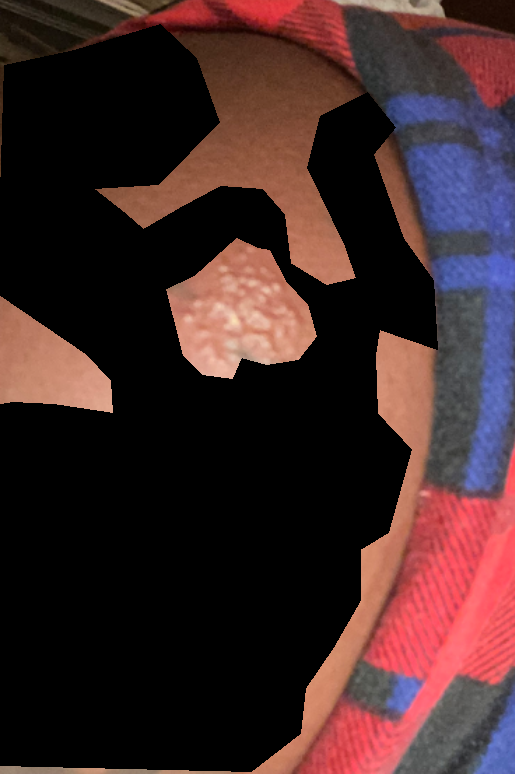The condition could not be reliably identified from the image. The patient reports pain. The arm is involved. Skin tone: human graders estimated MST 6 or 7. No associated systemic symptoms reported. Female contributor, age 18–29. The photograph is a close-up of the affected area. The lesion is described as raised or bumpy. Reported duration is about one day.